A dermatoscopic image of a skin lesion; a male patient aged 28 to 32: 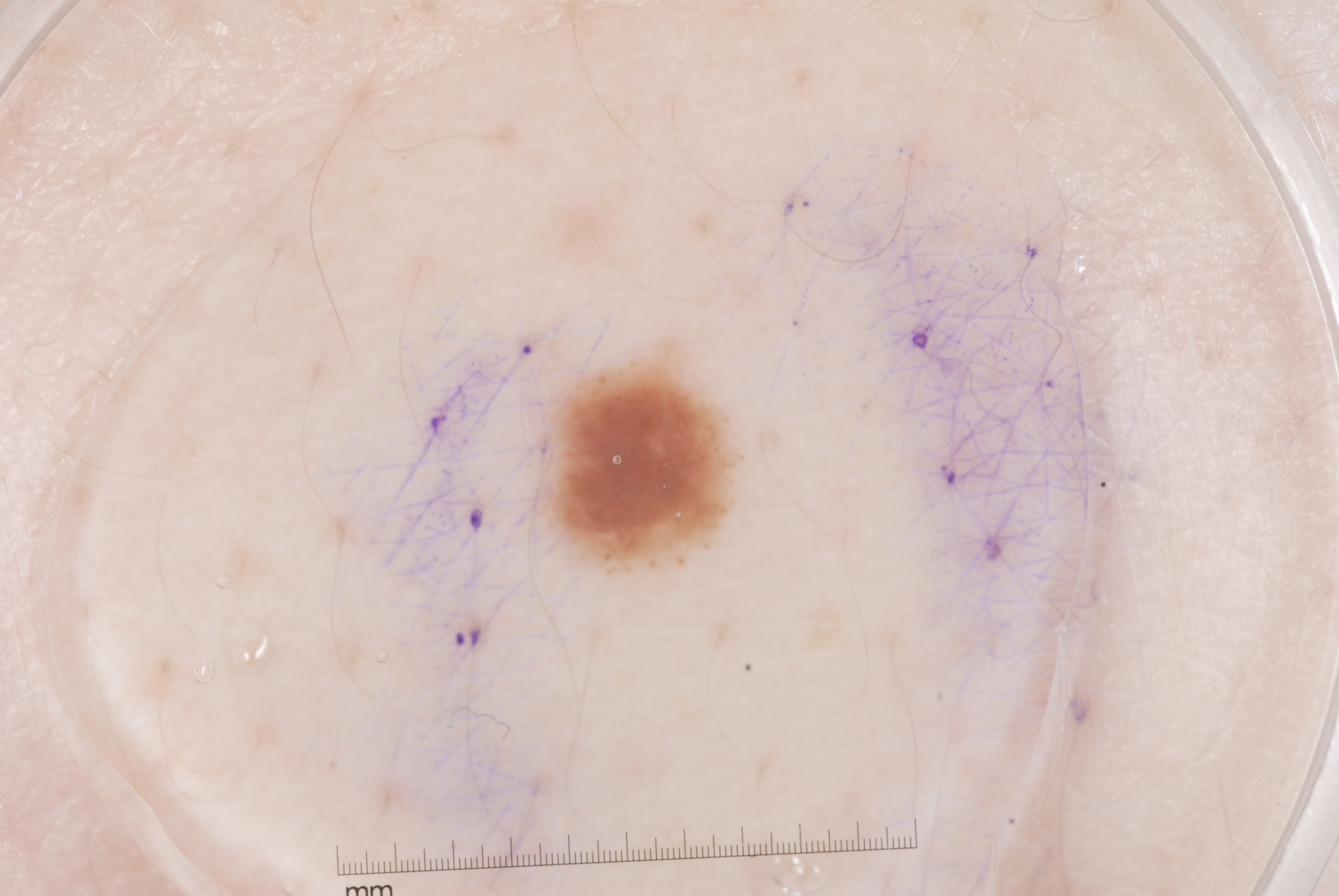Summary: The lesion takes up about 3% of the image. Dermoscopic assessment notes milia-like cysts and pigment network. As (left, top, right, bottom), the lesion spans 555, 357, 732, 574. Assessment: Clinically diagnosed as a melanocytic nevus, a benign skin lesion.